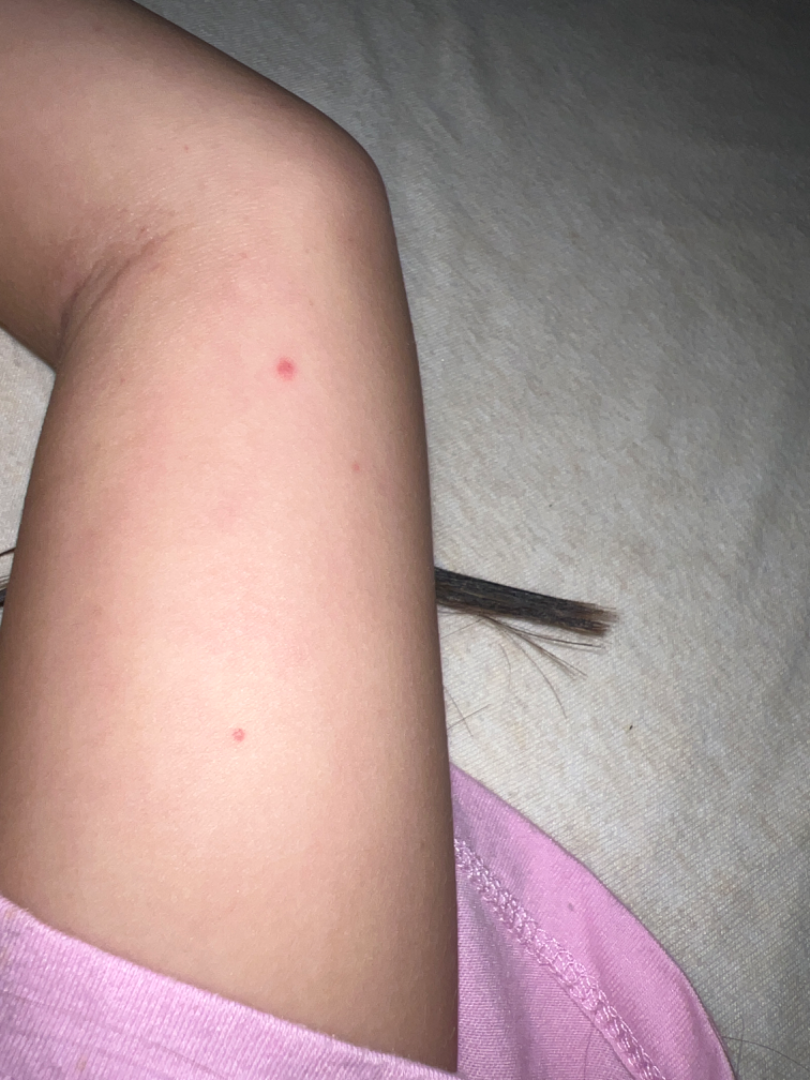| feature | finding |
|---|---|
| skin tone | Fitzpatrick phototype III; non-clinician graders estimated Monk skin tone scale 2 or 3 |
| image framing | at a distance |
| diagnostic considerations | single-reviewer assessment: favoring Acne; the differential also includes Perioral Dermatitis |